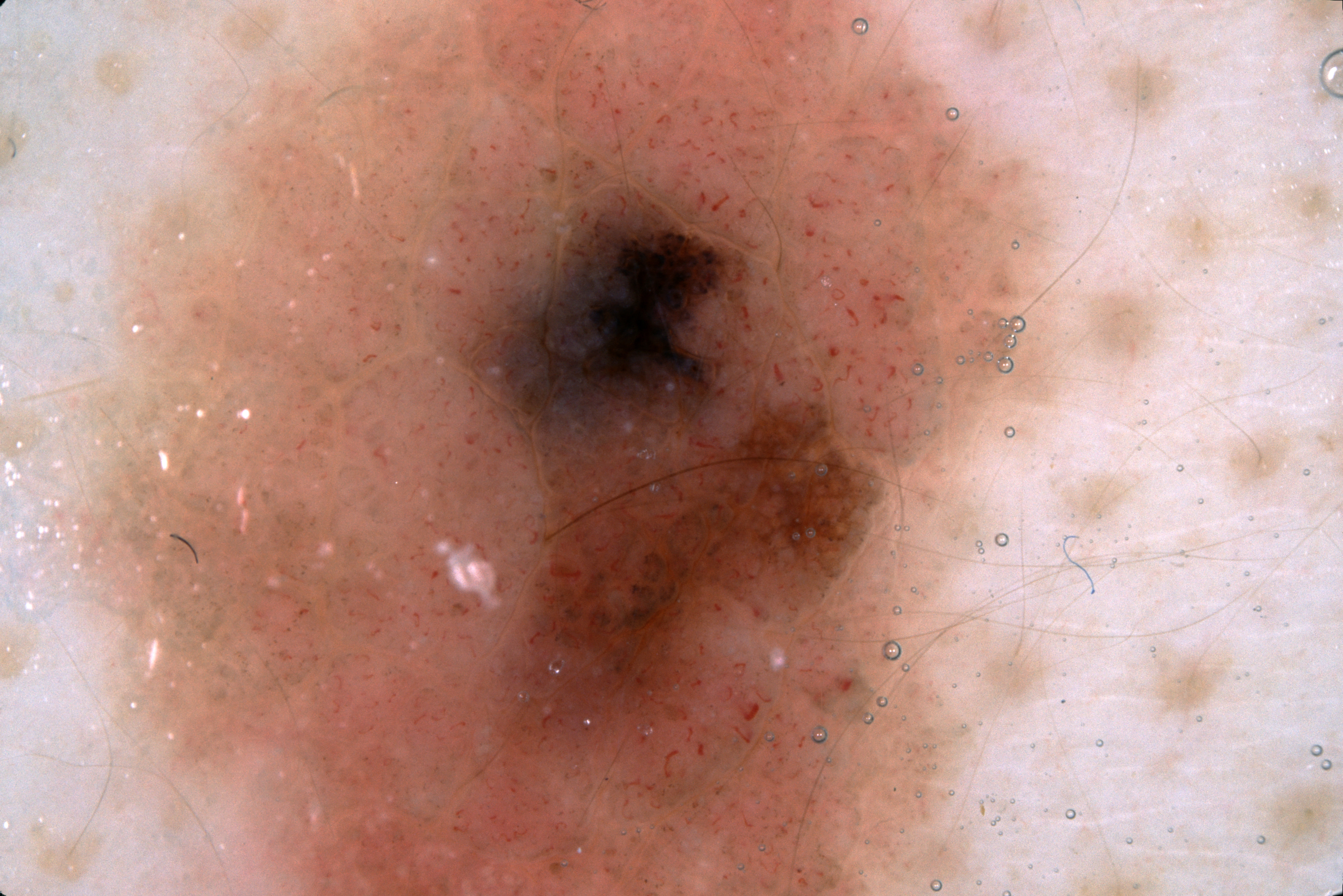A female patient. A dermoscopic close-up of a skin lesion. With coordinates (x1, y1, x2, y2), the visible lesion spans [73, 0, 1077, 895]. The dermoscopic pattern shows no negative network, pigment network, streaks, or milia-like cysts. Diagnosed as a melanocytic nevus, a benign lesion.